A dermoscopic photograph of a skin lesion.
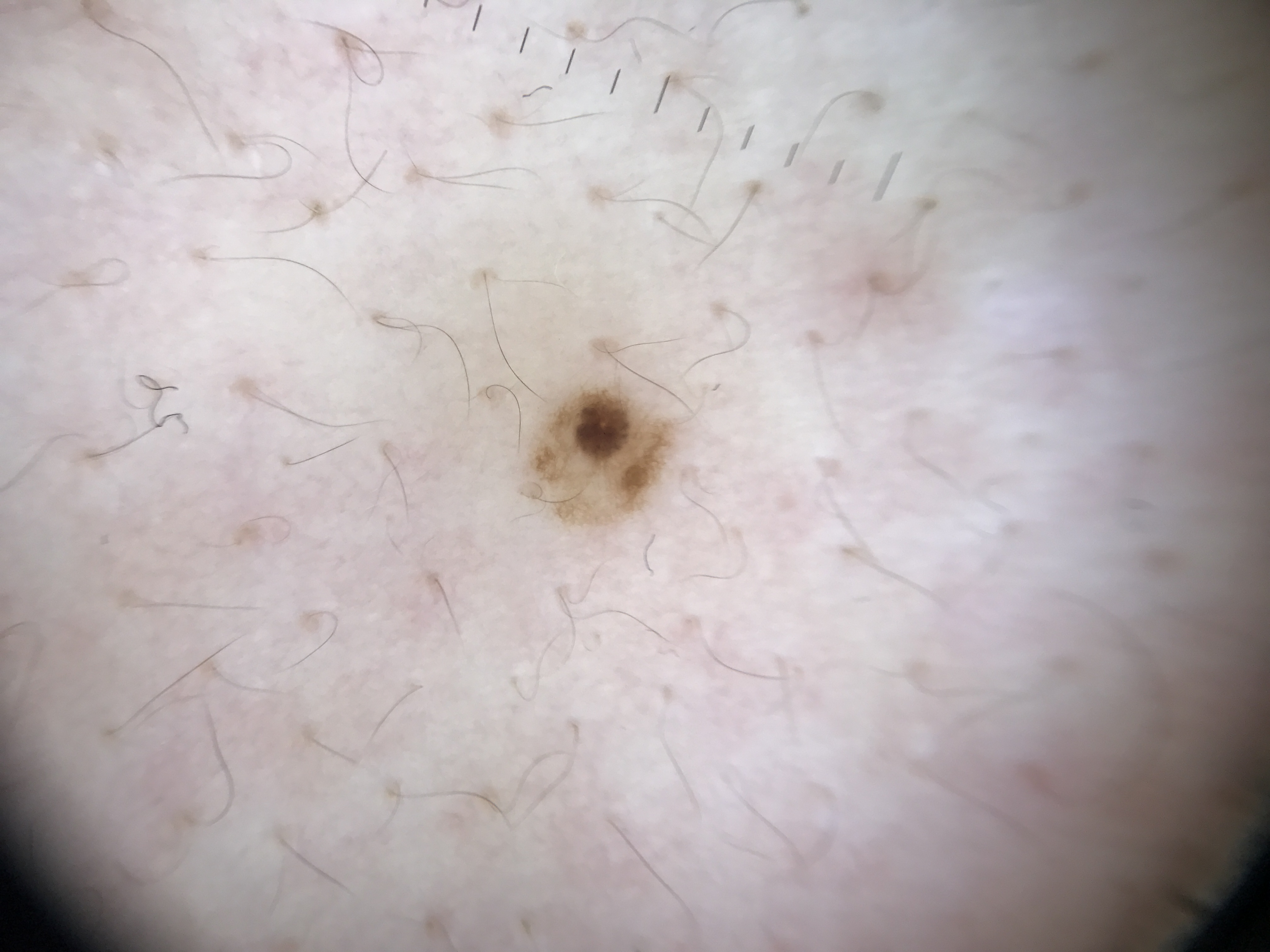| field | value |
|---|---|
| class | dysplastic junctional nevus (expert consensus) |